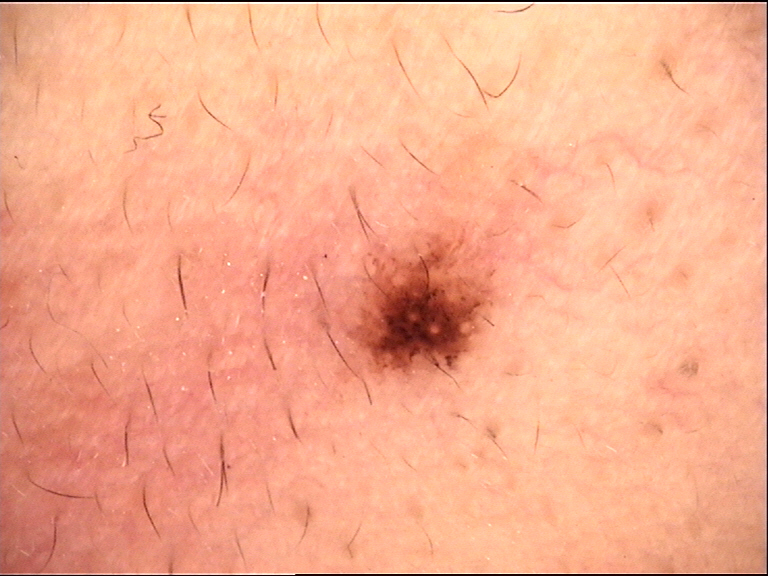A dermatoscopic image of a skin lesion. This is a compound, banal lesion. Classified as a Miescher nevus.